The lesion is described as rough or flaky and flat · Fitzpatrick skin type III; lay reviewers estimated Monk Skin Tone 3 or 5 · the subject is 30–39, female · the lesion is associated with bothersome appearance · the affected area is the leg · reported duration is three to twelve months · self-categorized by the patient as a pigmentary problem · the photograph is a close-up of the affected area:
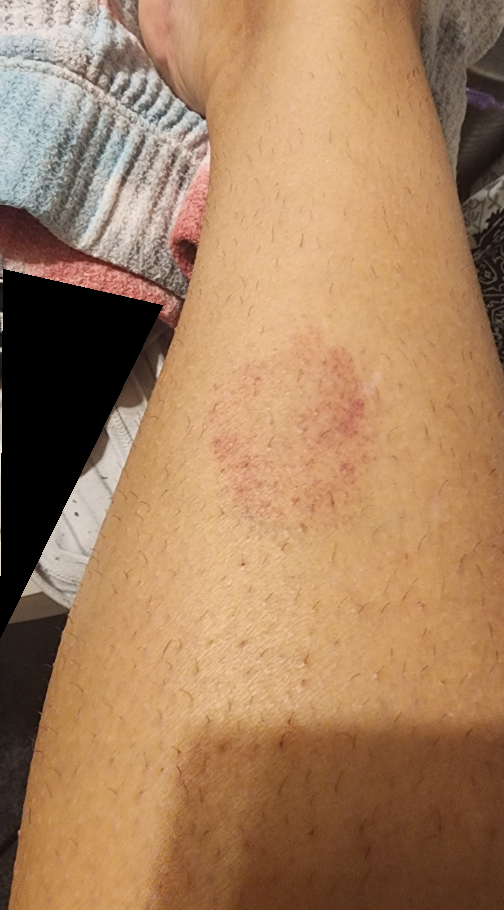On remote dermatologist review, Purpura (weight 0.54); Hemangioma (weight 0.23); Drug Rash (weight 0.23).